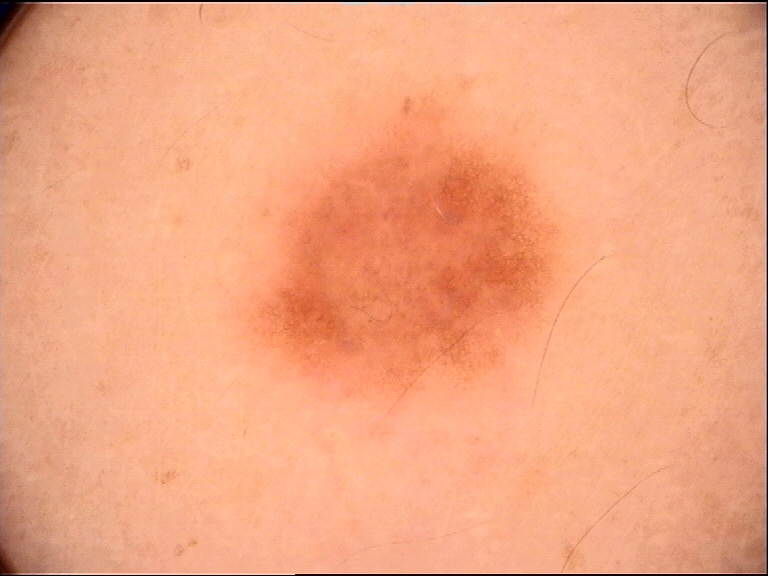Conclusion: The diagnostic label was a dysplastic junctional nevus.